A female subject in their early 70s · a clinical photograph showing a skin lesion:
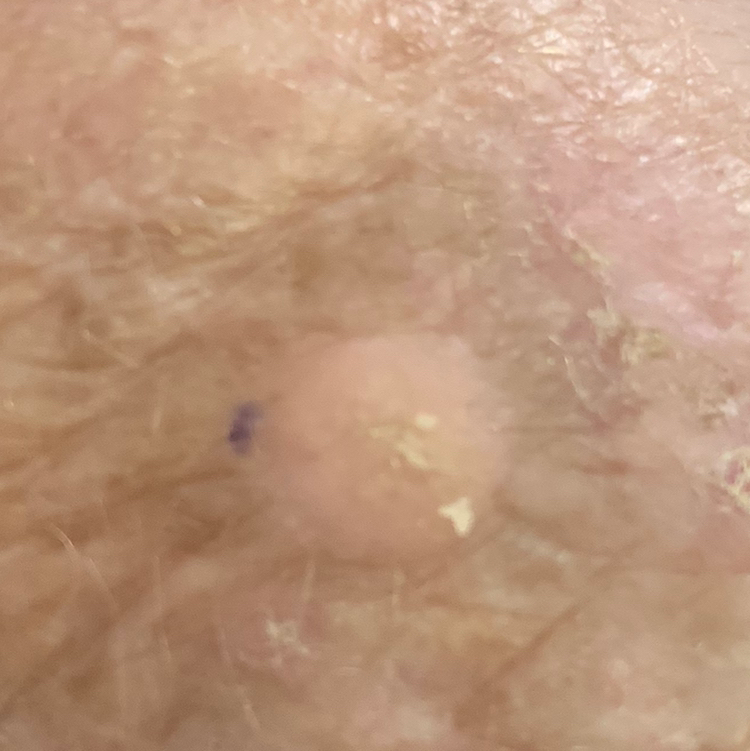Q: Where on the body is the lesion?
A: a hand
Q: What did the workup show?
A: actinic keratosis (biopsy-proven)